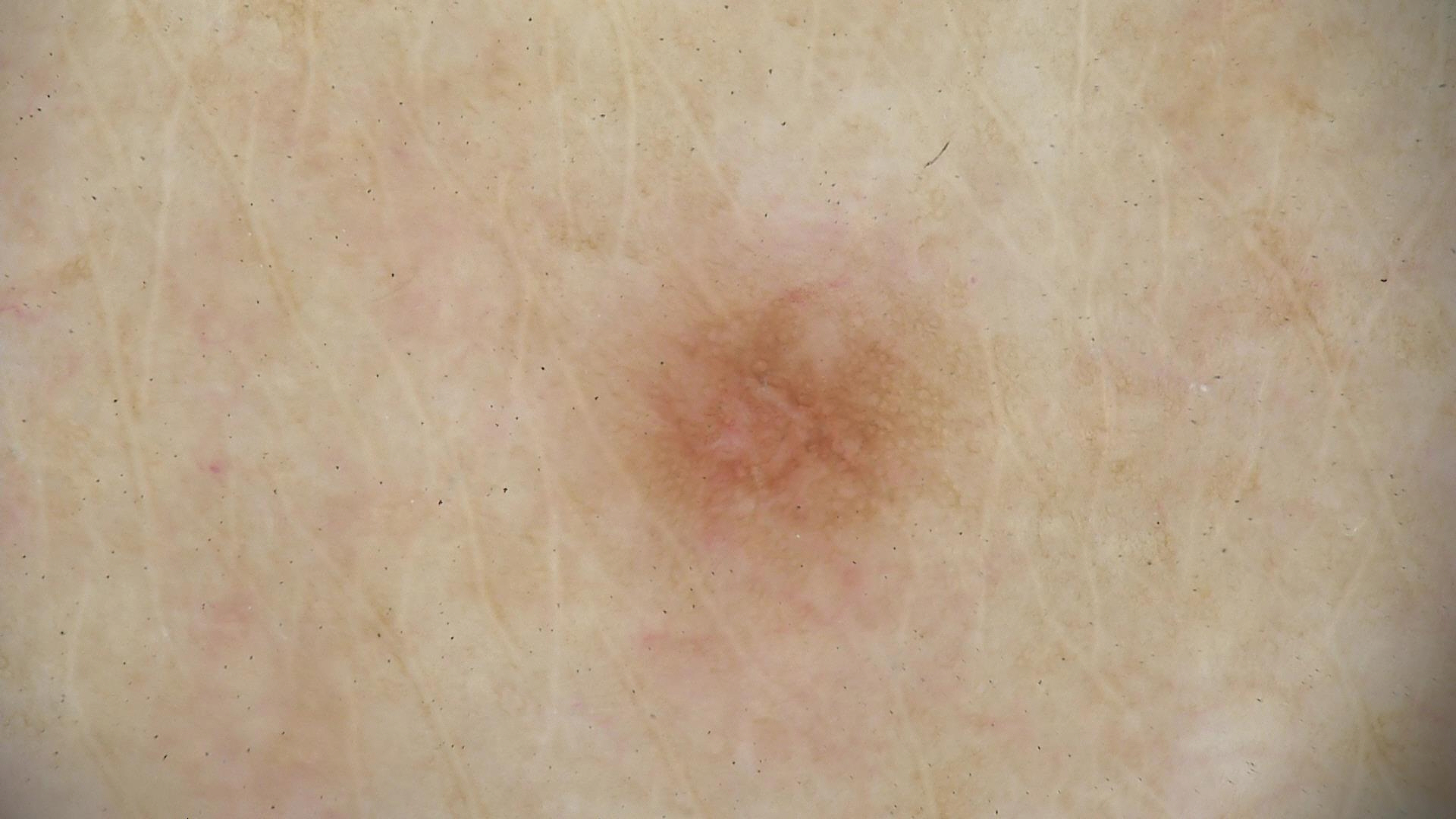• diagnostic label — dysplastic junctional nevus (expert consensus)